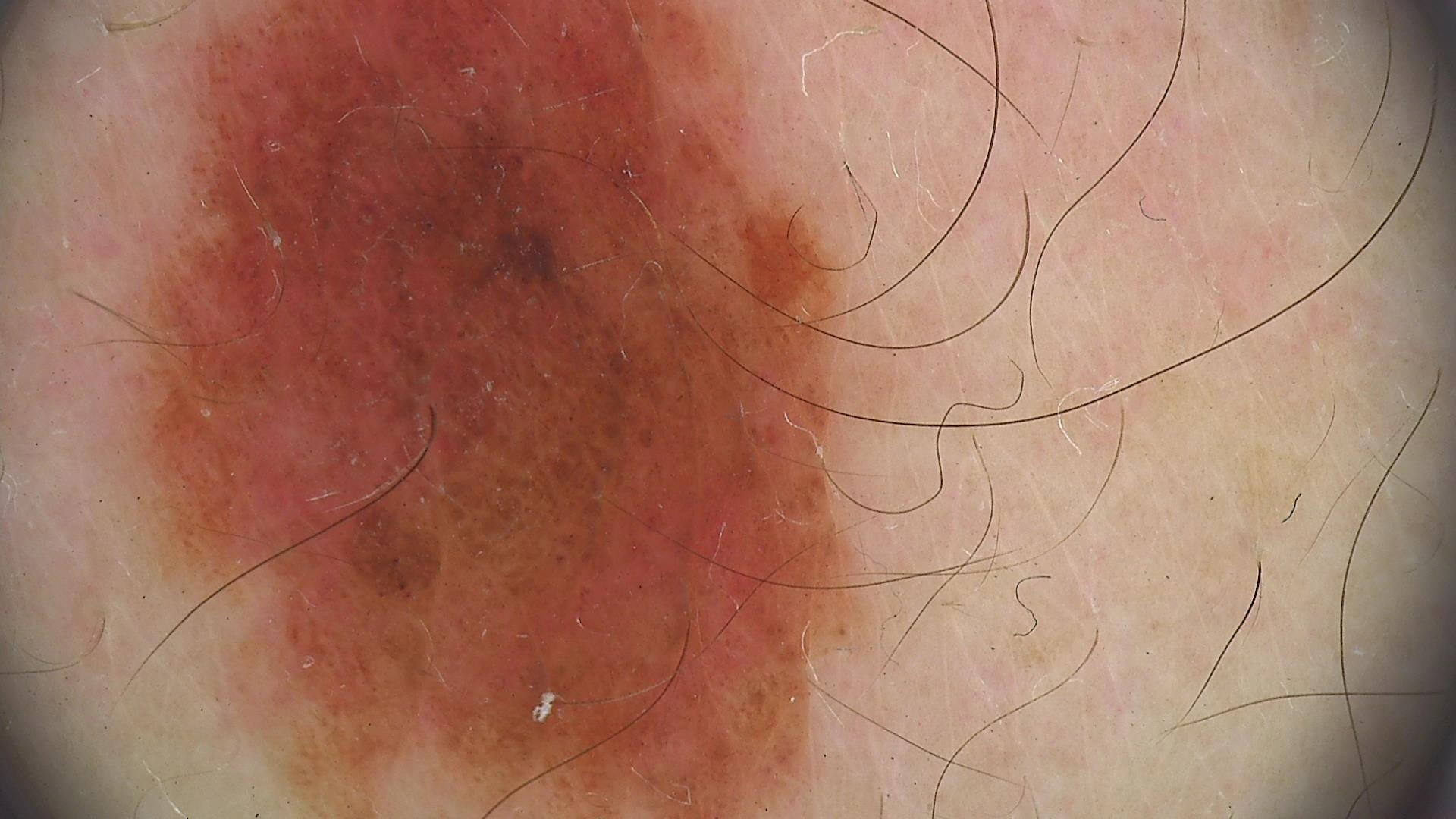assessment = dysplastic junctional nevus (expert consensus).